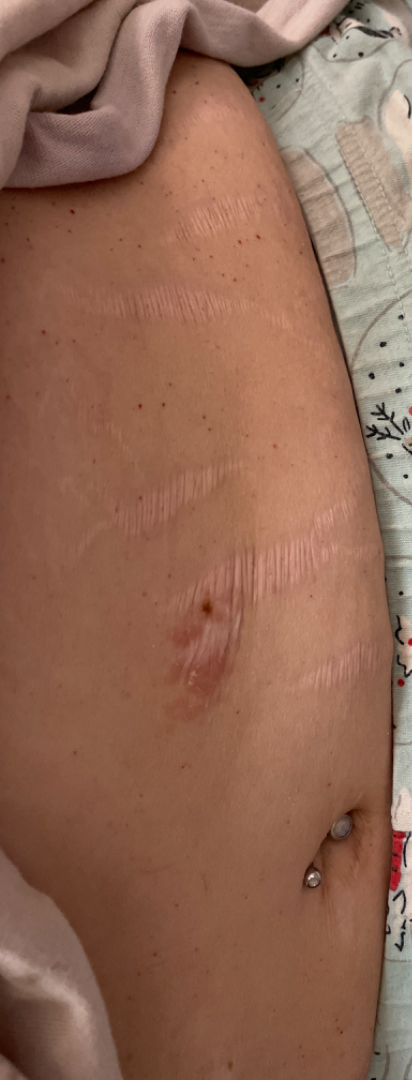<case>
<assessment>not assessable</assessment>
<symptoms>bothersome appearance</symptoms>
<texture>raised or bumpy</texture>
<shot_type>at a distance</shot_type>
<patient>female, age 40–49</patient>
<patient_category>a rash</patient_category>
<body_site>front of the torso</body_site>
<duration>one to four weeks</duration>
</case>